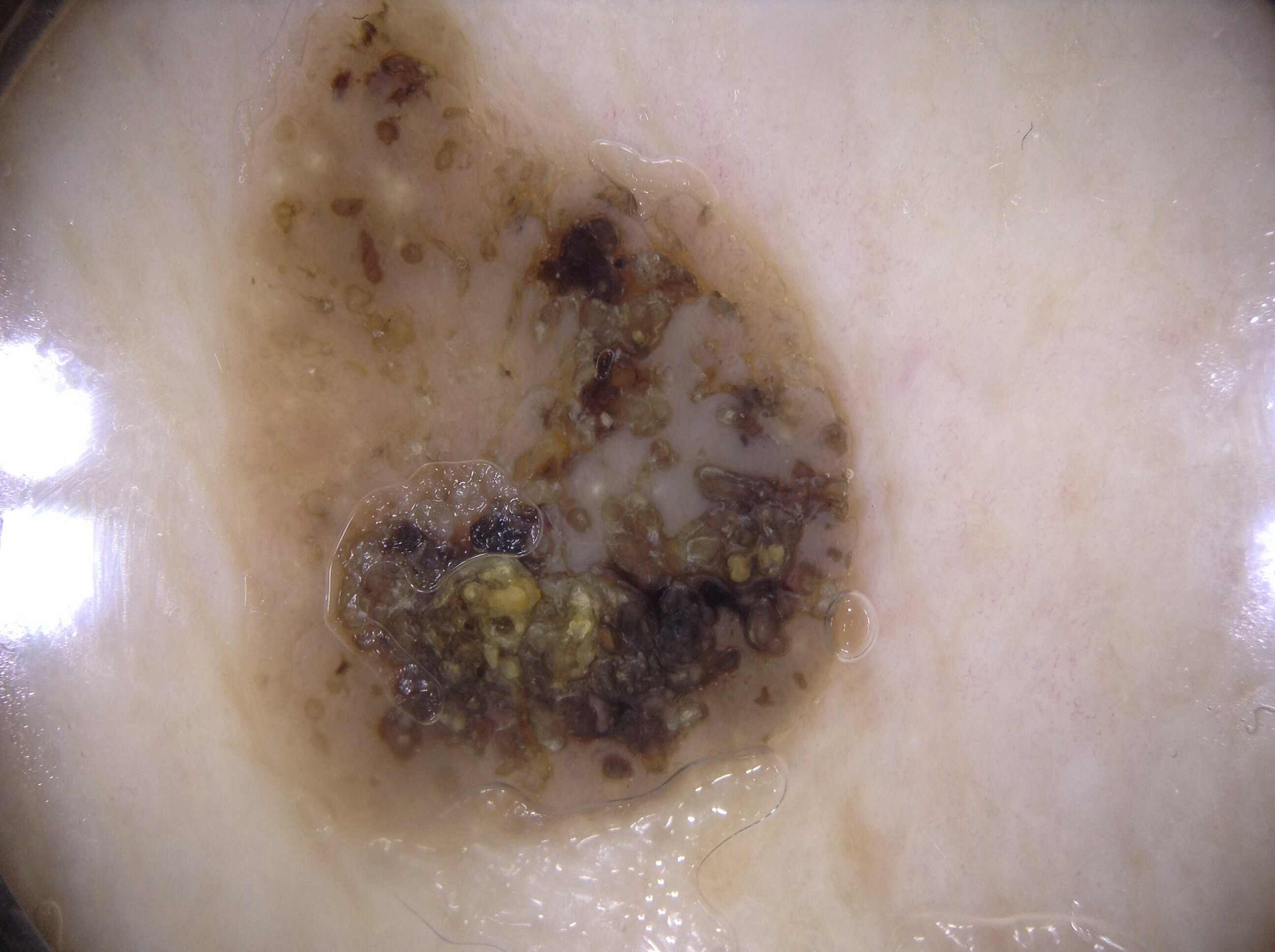* subject — male, aged around 85 or older
* modality — dermoscopy
* bounding box — x1=210 y1=0 x2=877 y2=855
* dermoscopic features — milia-like cysts; absent: pigment network, streaks, and negative network
* lesion extent — large
* lesion margin — extends past the field edge
* diagnosis — a seborrheic keratosis, a benign skin lesion